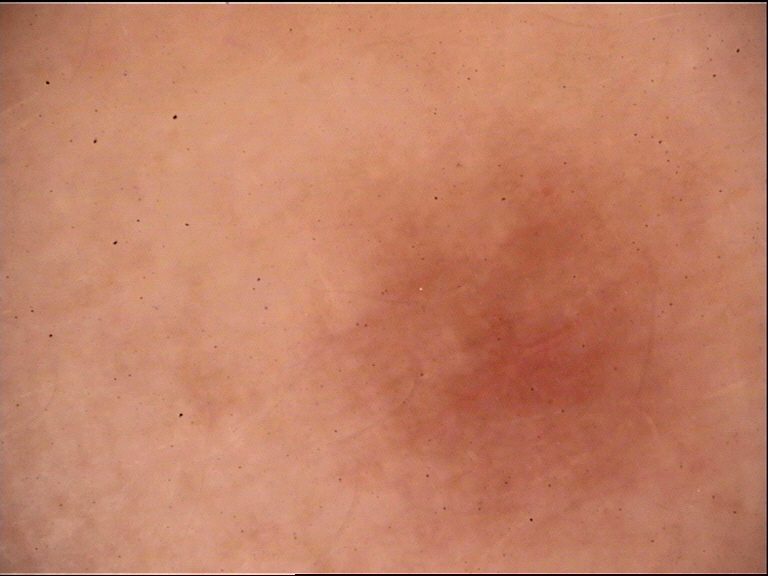Q: What is this lesion?
A: dermatofibroma (expert consensus)